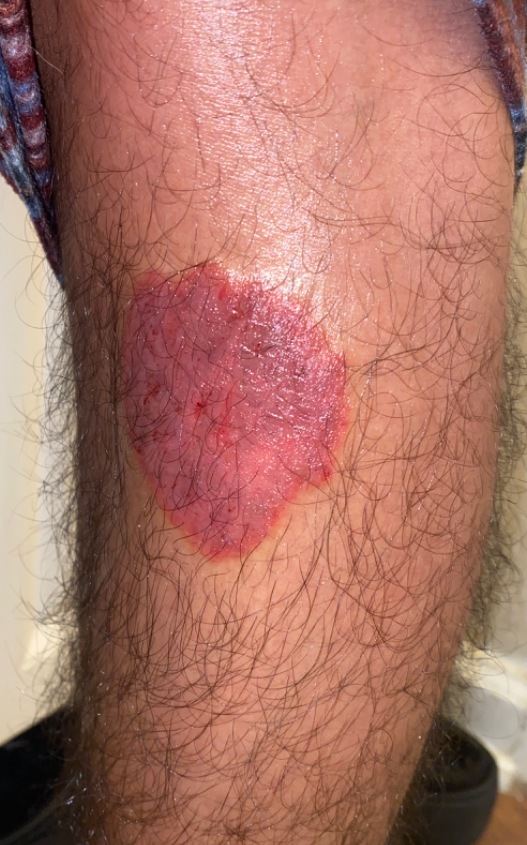The skin condition could not be confidently assessed from this image. Texture is reported as rough or flaky and flat. Present for three to twelve months. Close-up view. The patient described the issue as a rash.